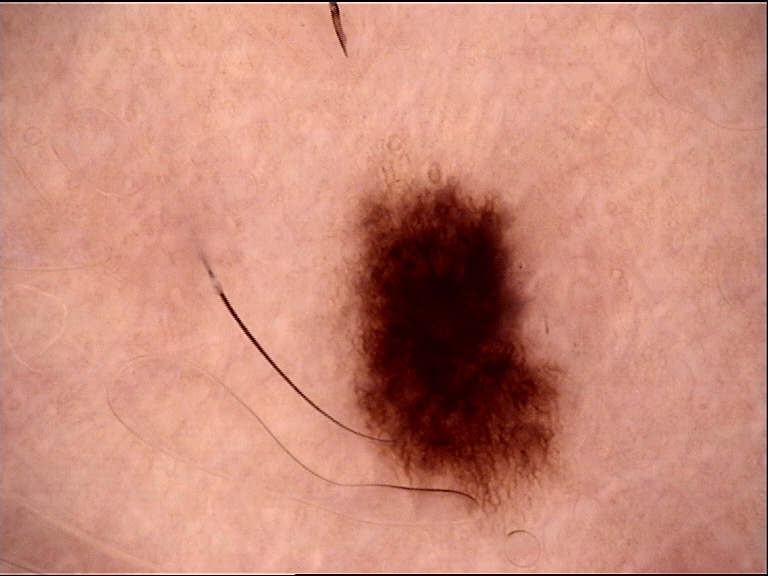image: dermatoscopy
lesion_type:
  main_class: banal
  pattern: junctional
diagnosis:
  name: junctional nevus
  code: jb
  malignancy: benign
  super_class: melanocytic
  confirmation: expert consensus